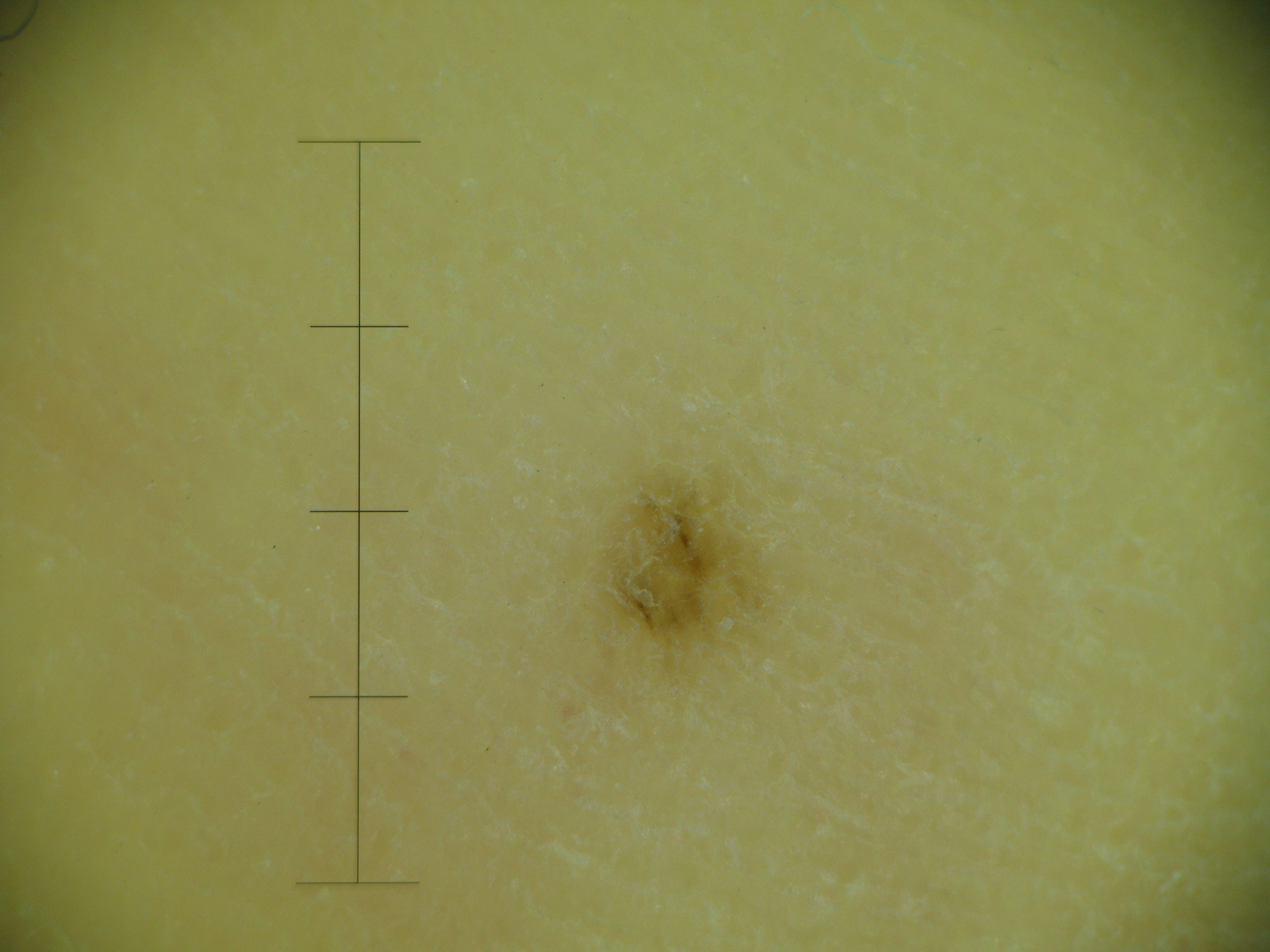Case:
A dermoscopic image of a skin lesion.
Impression:
Labeled as a banal lesion — an acral junctional nevus.